Reported duration is about one day, a close-up photograph, the affected area is the head or neck, the patient considered this a rash:
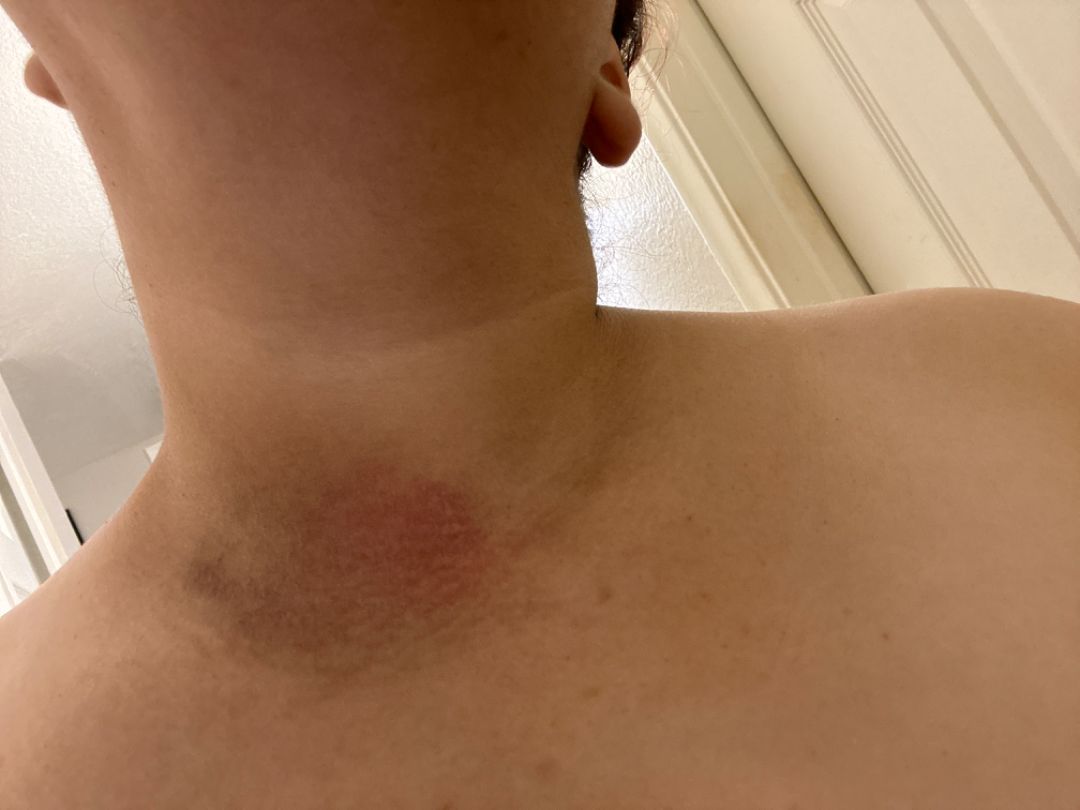Assessment:
On photographic review: the leading impression is ecchymoses; an alternative is Eczema.